A male subject aged 15; a dermoscopy image of a skin lesion; referred with a clinical suspicion of melanocytic nevus; few moles overall by the patient's own estimate.
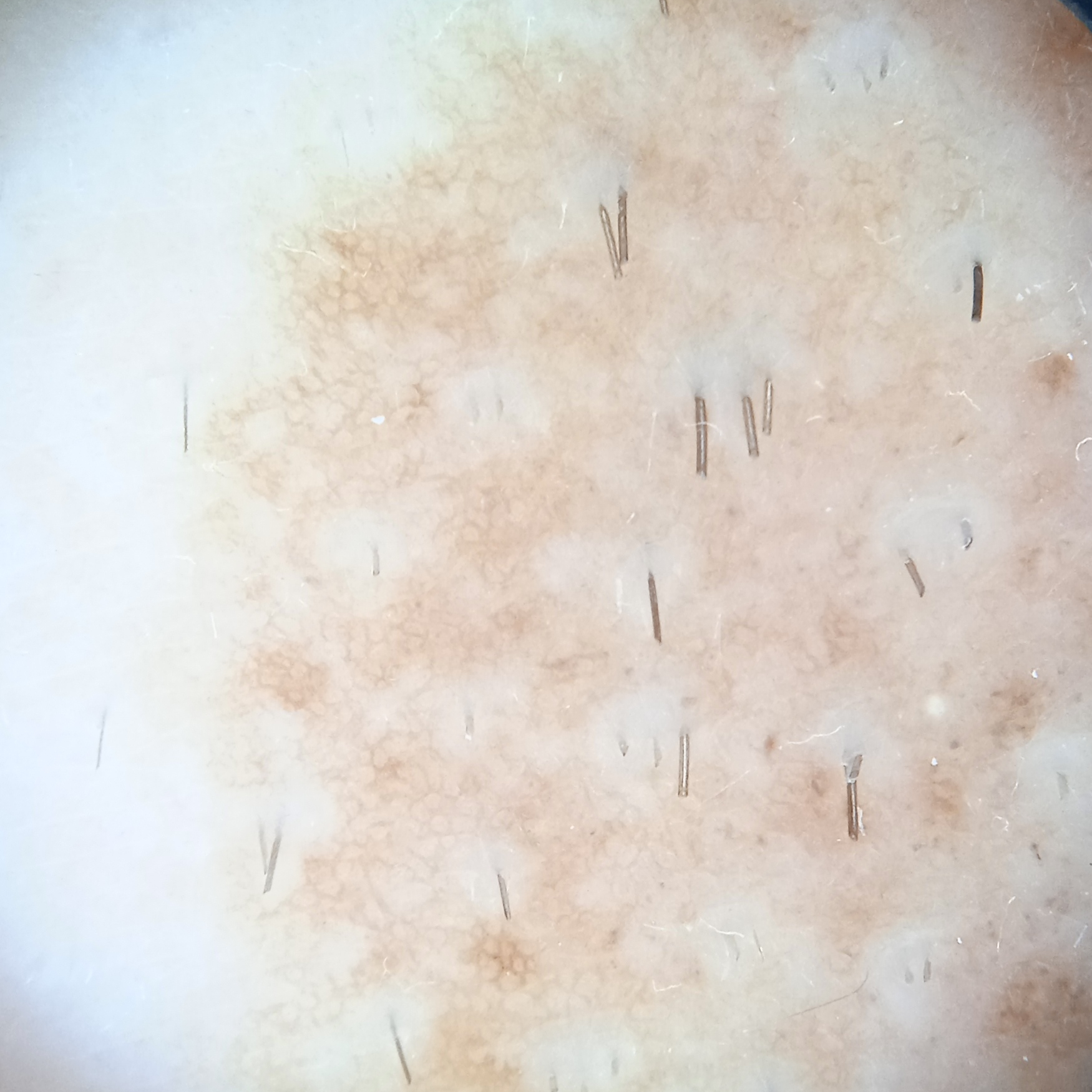Findings:
The lesion measures approximately 26.1 mm.
Diagnosis:
Histopathologically confirmed as a melanocytic nevus, following a punch biopsy.